A dermatoscopic image of a skin lesion.
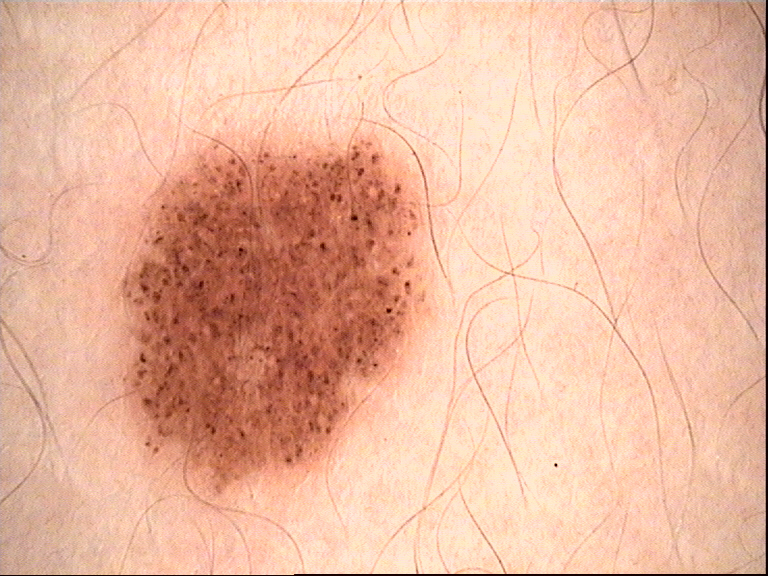The diagnostic label was a dysplastic junctional nevus.